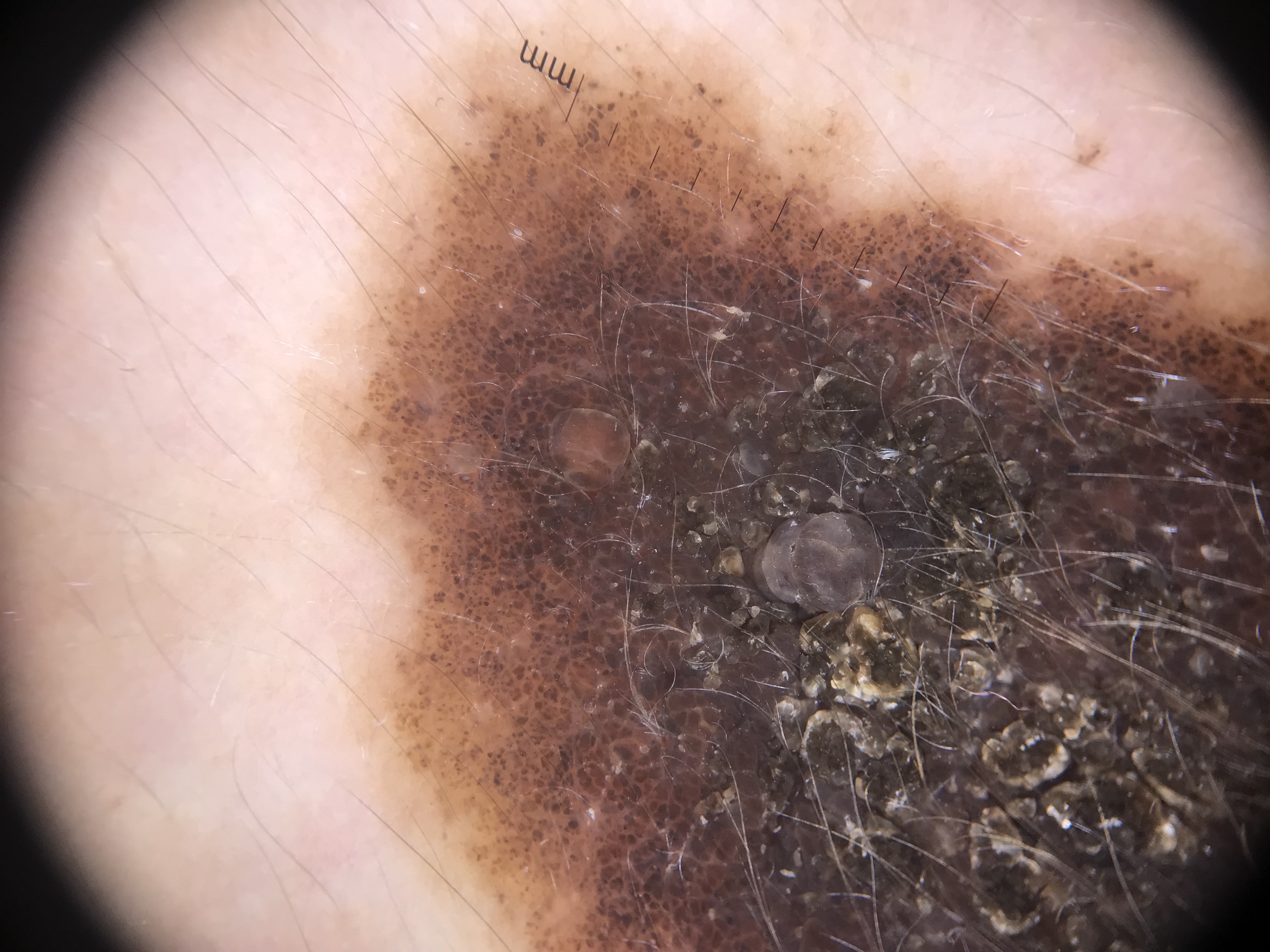Q: What is the imaging modality?
A: dermatoscopy
Q: What was the diagnostic impression?
A: congenital compound nevus (expert consensus)